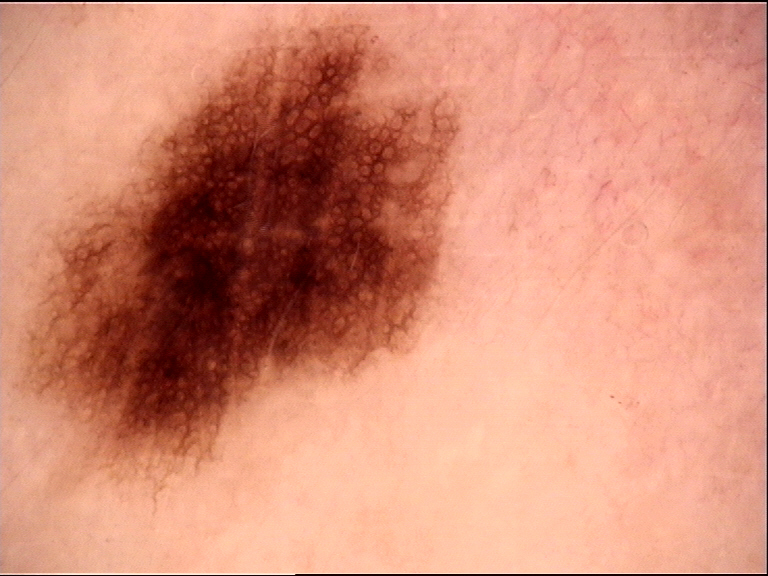A dermoscopy image of a single skin lesion. Diagnosed as a dysplastic junctional nevus.